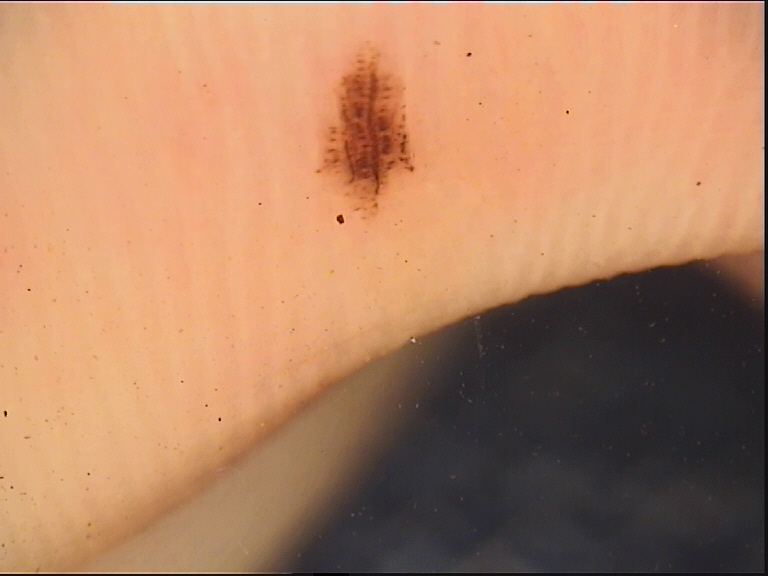diagnosis:
  name: acral dysplastic junctional nevus
  code: ajd
  malignancy: benign
  super_class: melanocytic
  confirmation: expert consensus